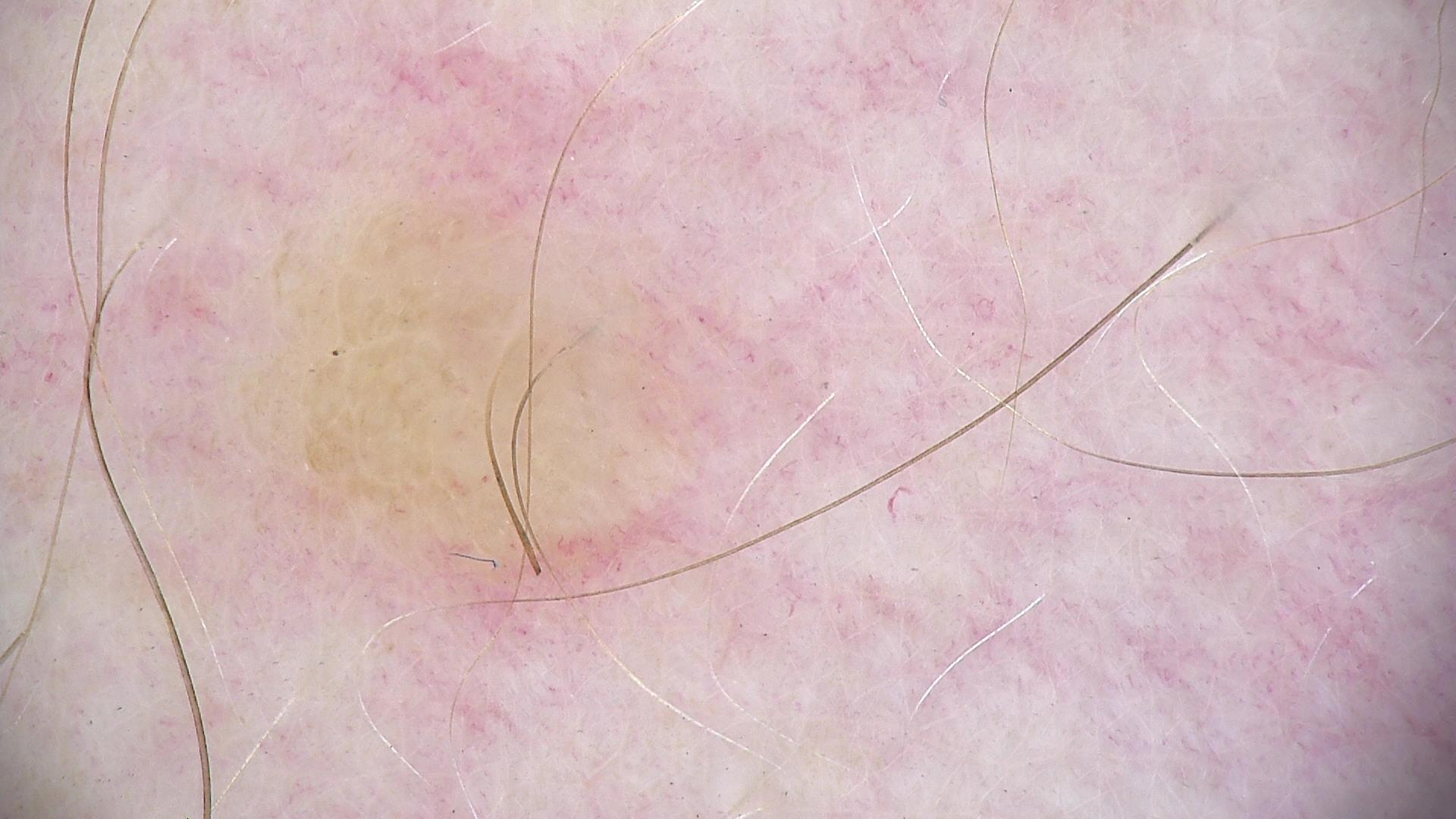diagnosis:
  name: dermal nevus
  code: db
  malignancy: benign
  super_class: melanocytic
  confirmation: expert consensus